A female subject 54 years of age; a clinical close-up of a skin lesion; acquired for a research image collection, with no referral diagnosis; the patient says their skin reddens with sun exposure:
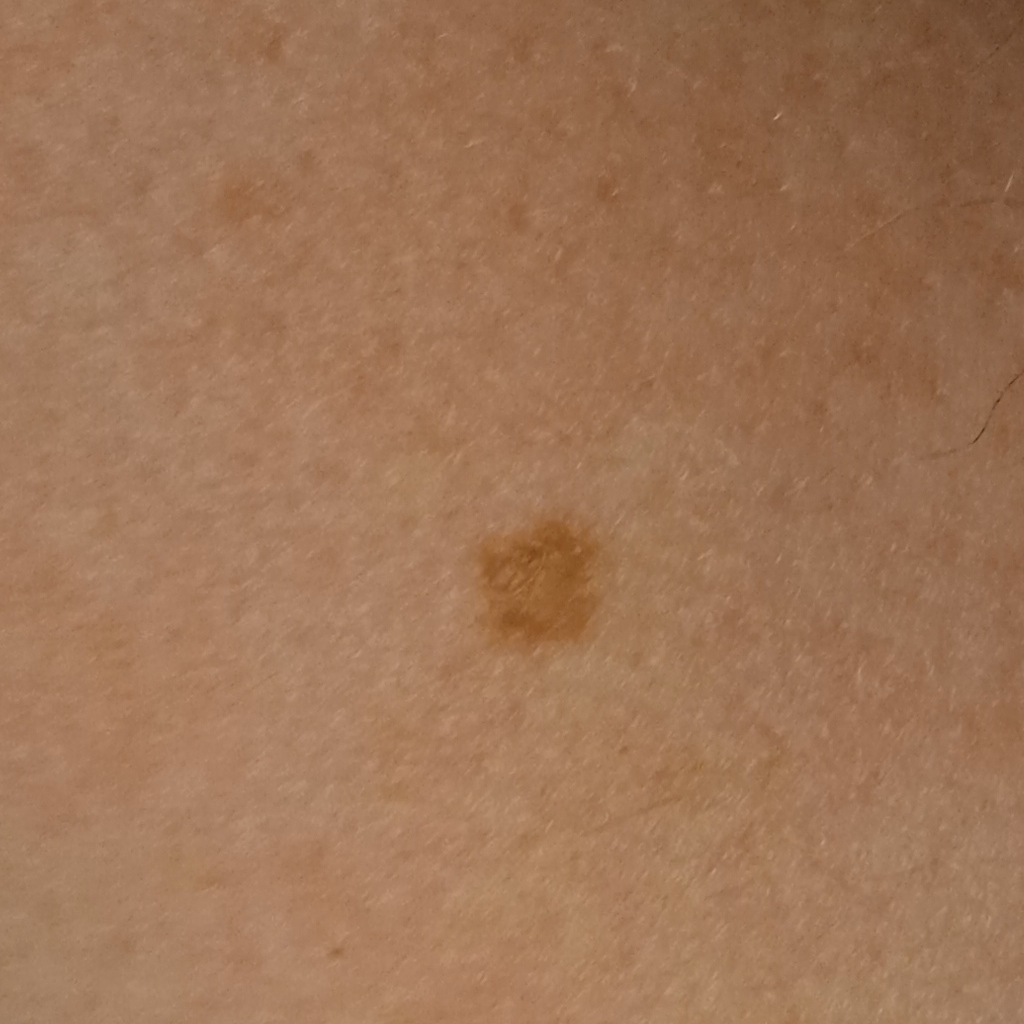Clinical context: Measuring roughly 4.7 mm. Assessment: The diagnostic impression was an atypical (dysplastic) nevus.